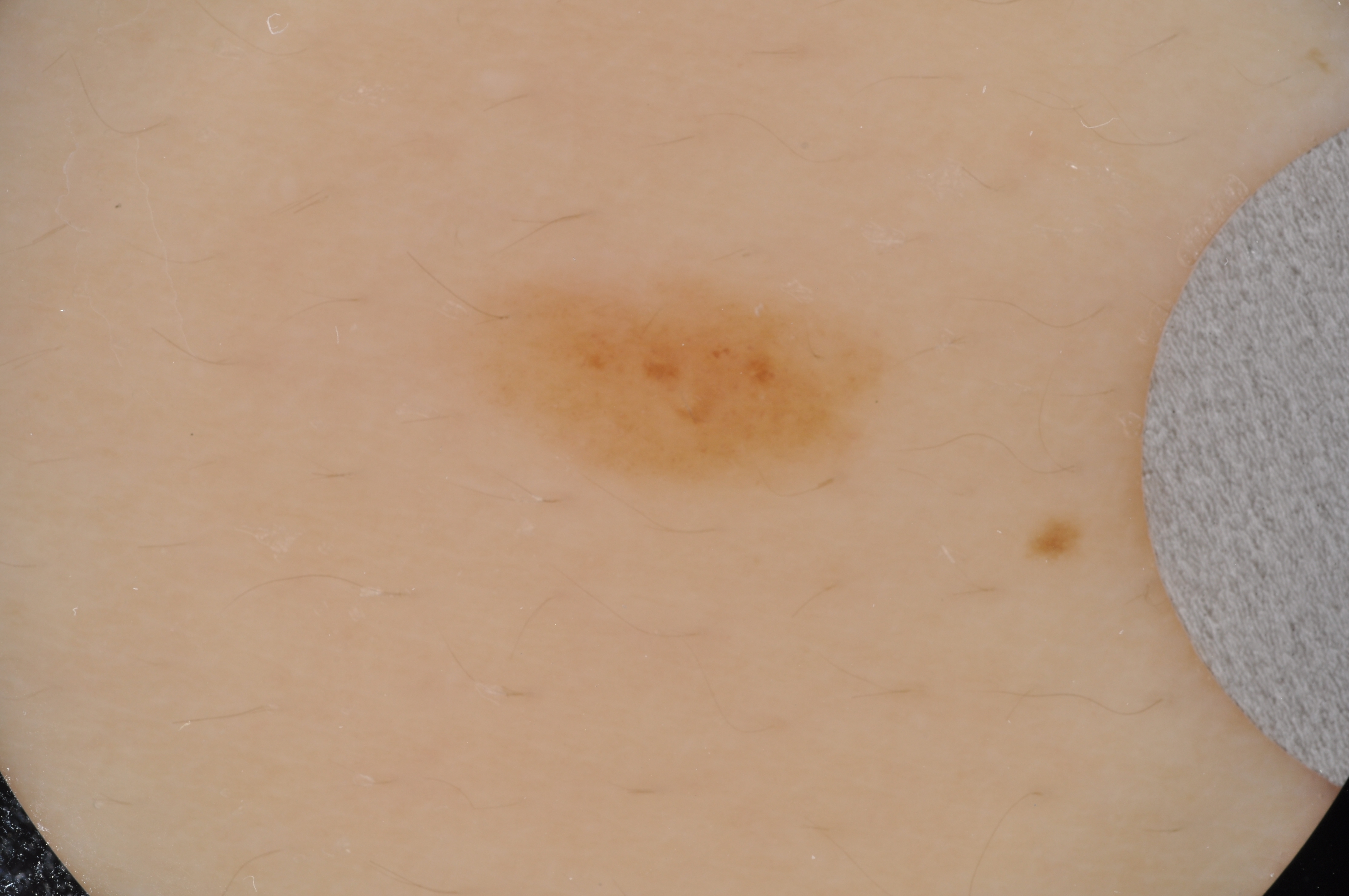A male patient approximately 15 years of age. A skin lesion imaged with a dermatoscope. Dermoscopy demonstrates no milia-like cysts, pigment network, globules, negative network, or streaks. With coordinates (x1, y1, x2, y2), the visible lesion spans bbox=[449, 265, 911, 505]. The lesion takes up about 7% of the image. The lesion was assessed as a melanocytic nevus.